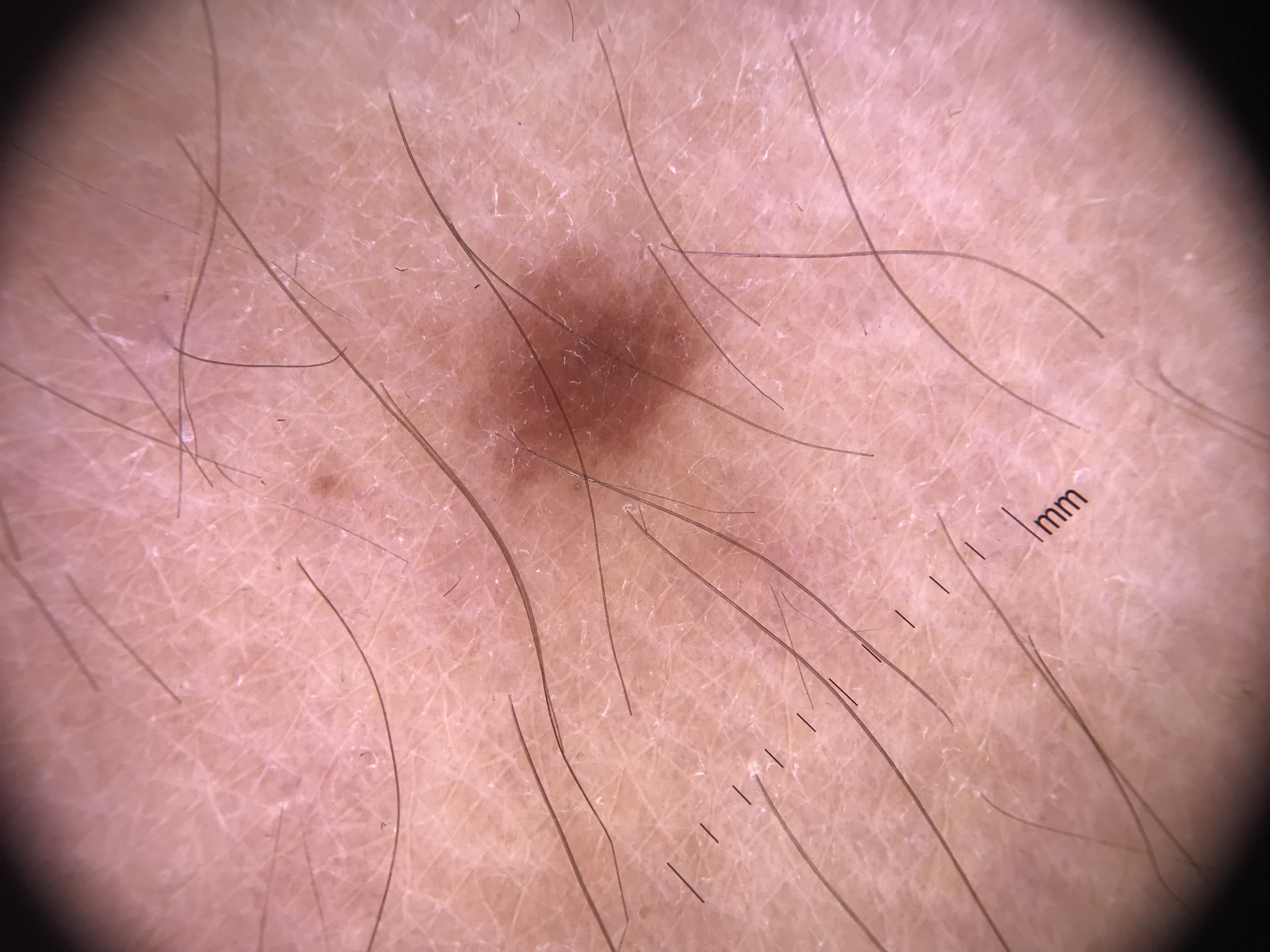Dermoscopy of a skin lesion. Consistent with a banal lesion — a junctional nevus.